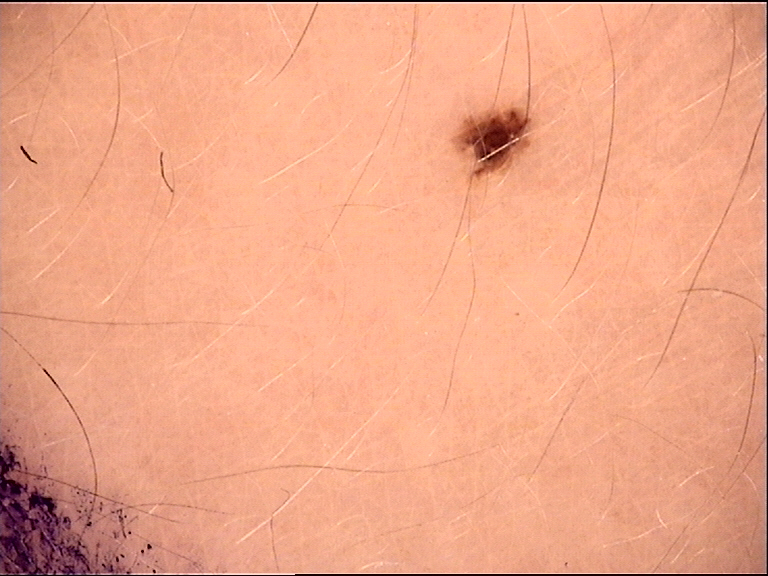A dermoscopic photograph of a skin lesion. Consistent with a benign lesion — a dysplastic junctional nevus.